A dermoscopic image of a skin lesion: 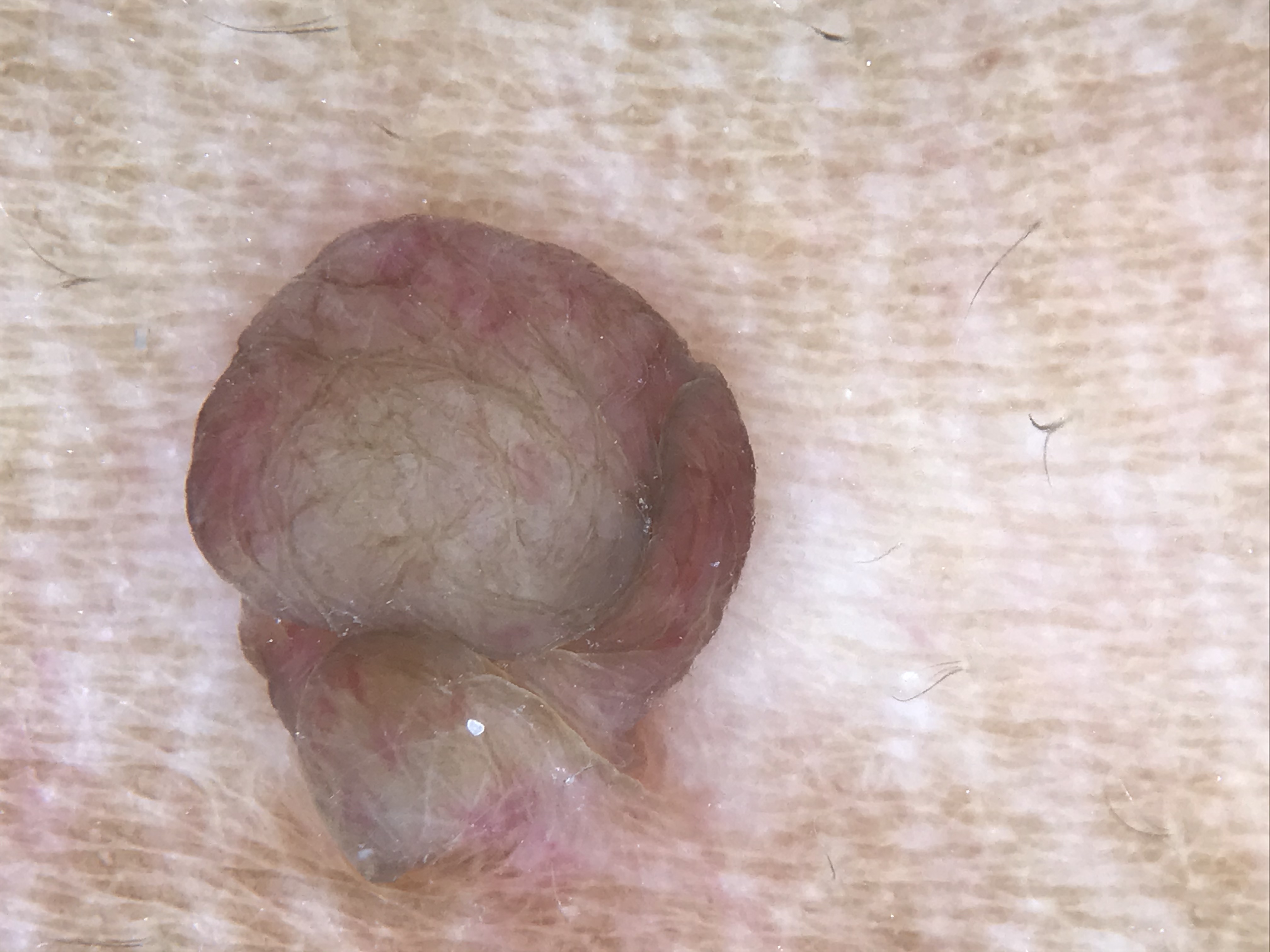label — dermal nevus (expert consensus)